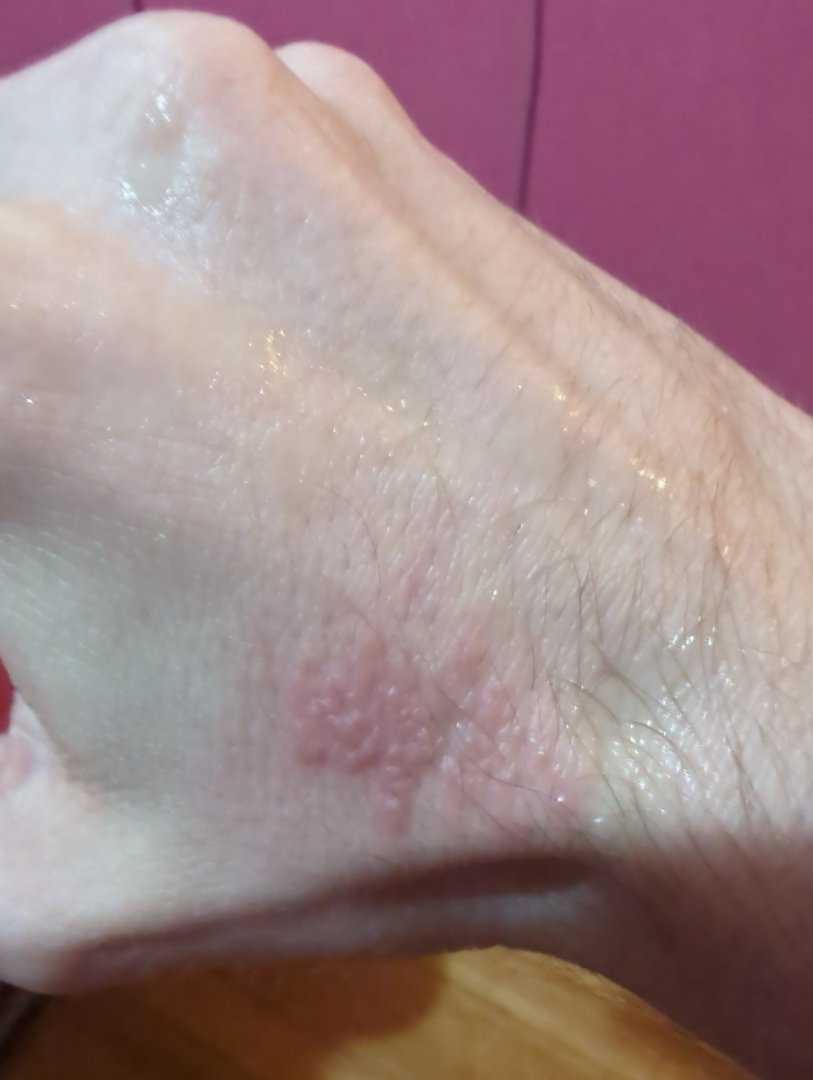The impression on review was Allergic Contact Dermatitis.